A skin lesion imaged with a dermatoscope.
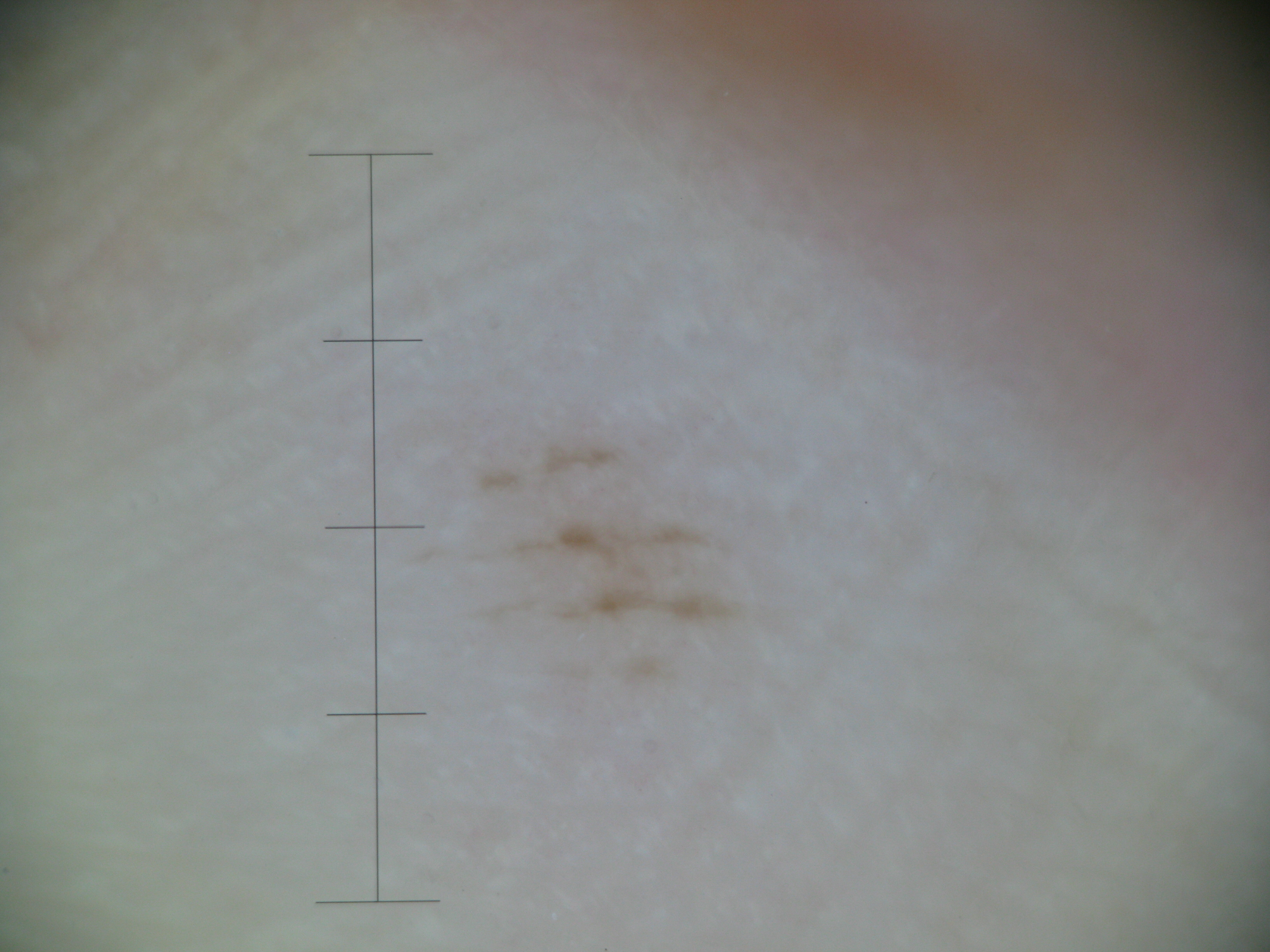This is a banal lesion. Classified as an acral junctional nevus.